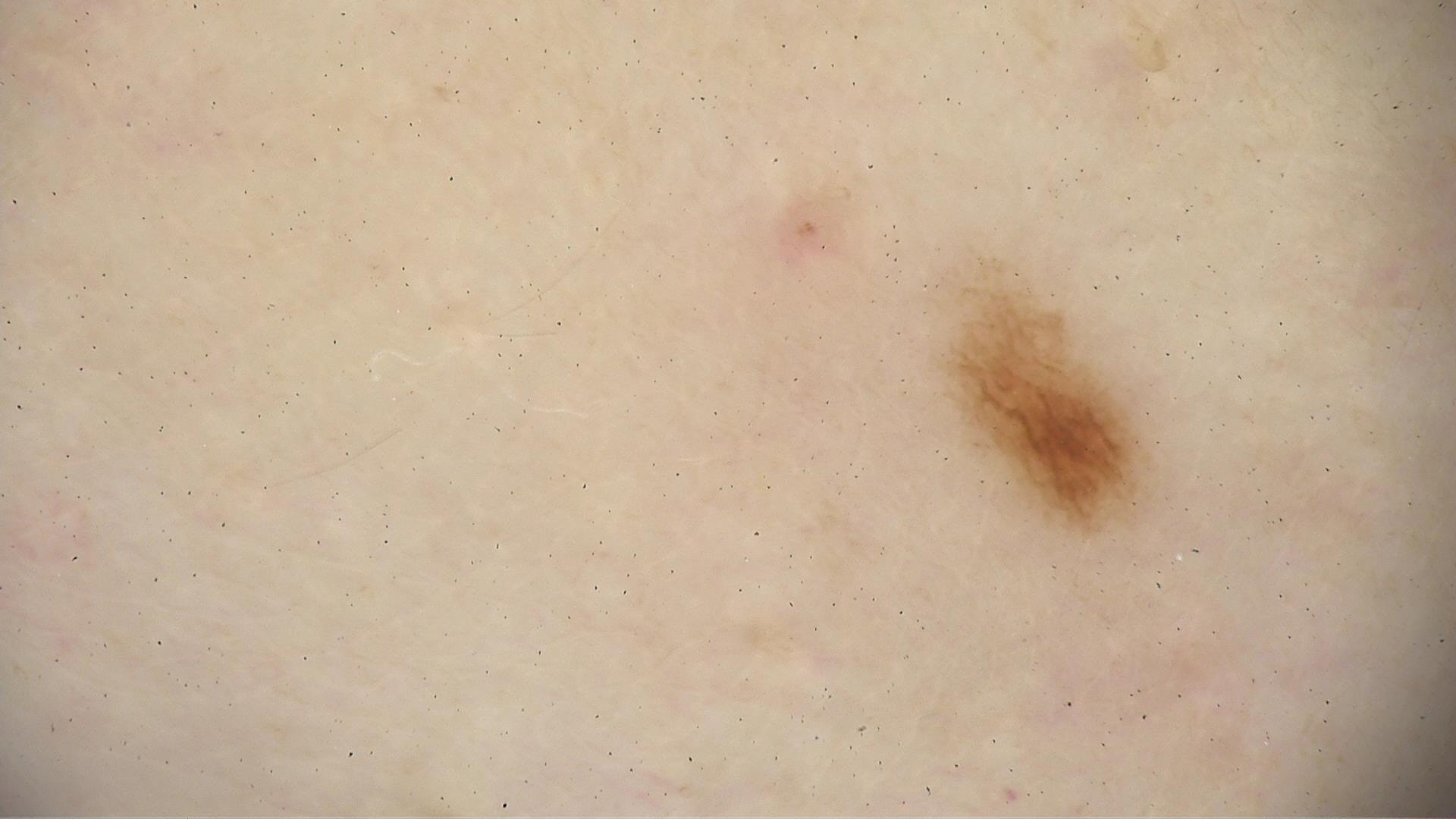Consistent with a dysplastic junctional nevus.